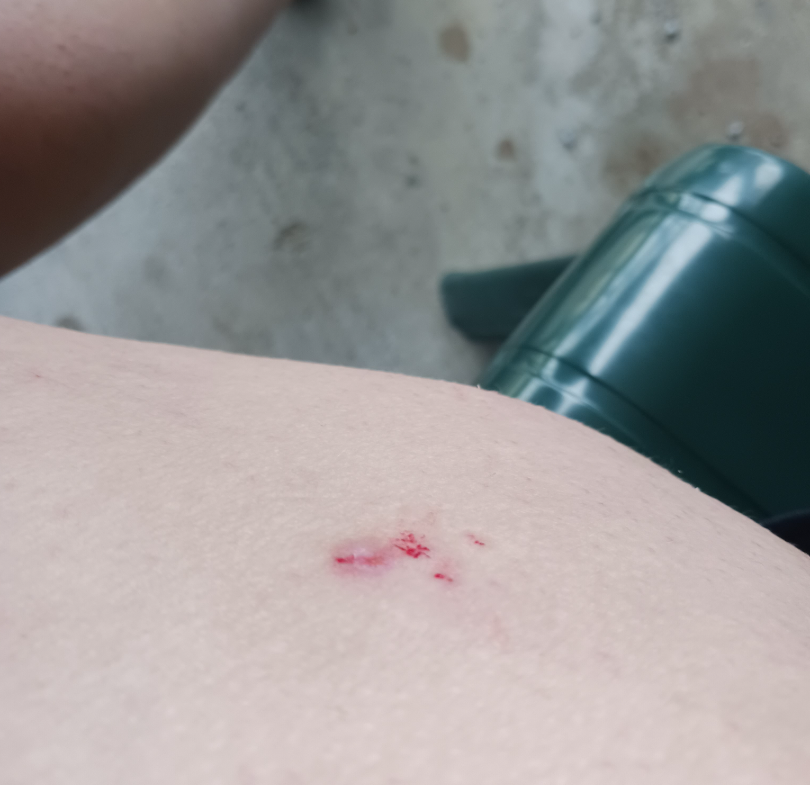<case>
  <duration>more than one year</duration>
  <patient>female, age 50–59</patient>
  <shot_type>at an angle</shot_type>
  <body_site>leg</body_site>
  <patient_category>a rash</patient_category>
  <texture>raised or bumpy</texture>
  <systemic_symptoms>none reported</systemic_symptoms>
  <symptoms>pain</symptoms>
  <differential>
    <leading>Insect Bite</leading>
    <unlikely>Lichen Simplex Chronicus; Eczema; Acute dermatitis, NOS; Erythema nodosum; Cutaneous sarcoidosis</unlikely>
  </differential>
</case>